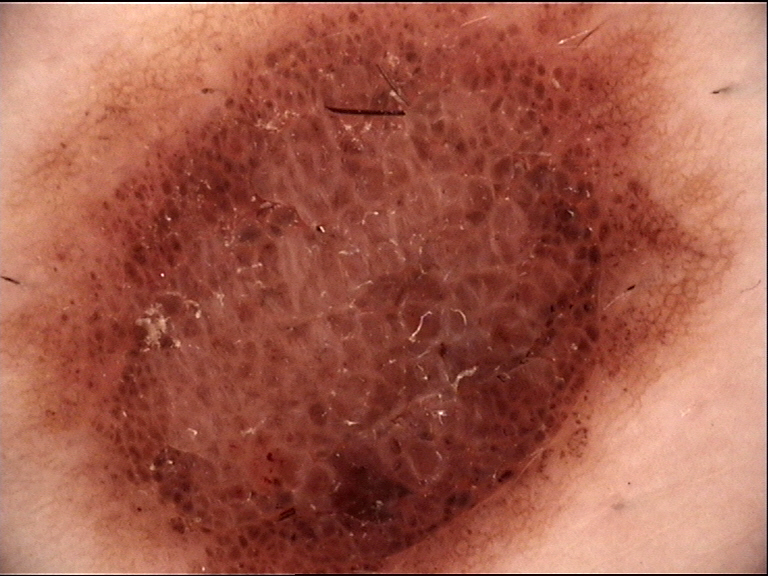category: banal; label: compound nevus (expert consensus).